A subject age 77; a smartphone photograph of a skin lesion:
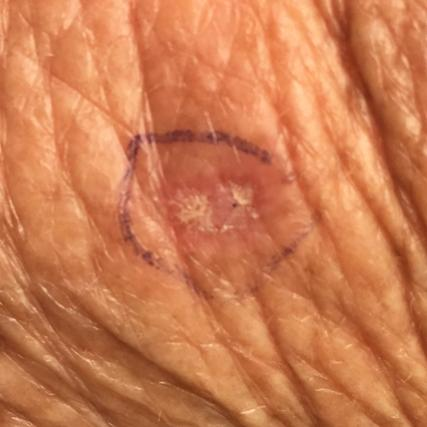The lesion is located on a forearm. The patient describes that the lesion itches. The diagnostic impression was an actinic keratosis.